The affected area is the leg and arm. Texture is reported as flat. The photo was captured at an angle. The patient reported no systemic symptoms. Skin tone: Fitzpatrick phototype III; non-clinician graders estimated MST 2. Reported duration is one to three months: 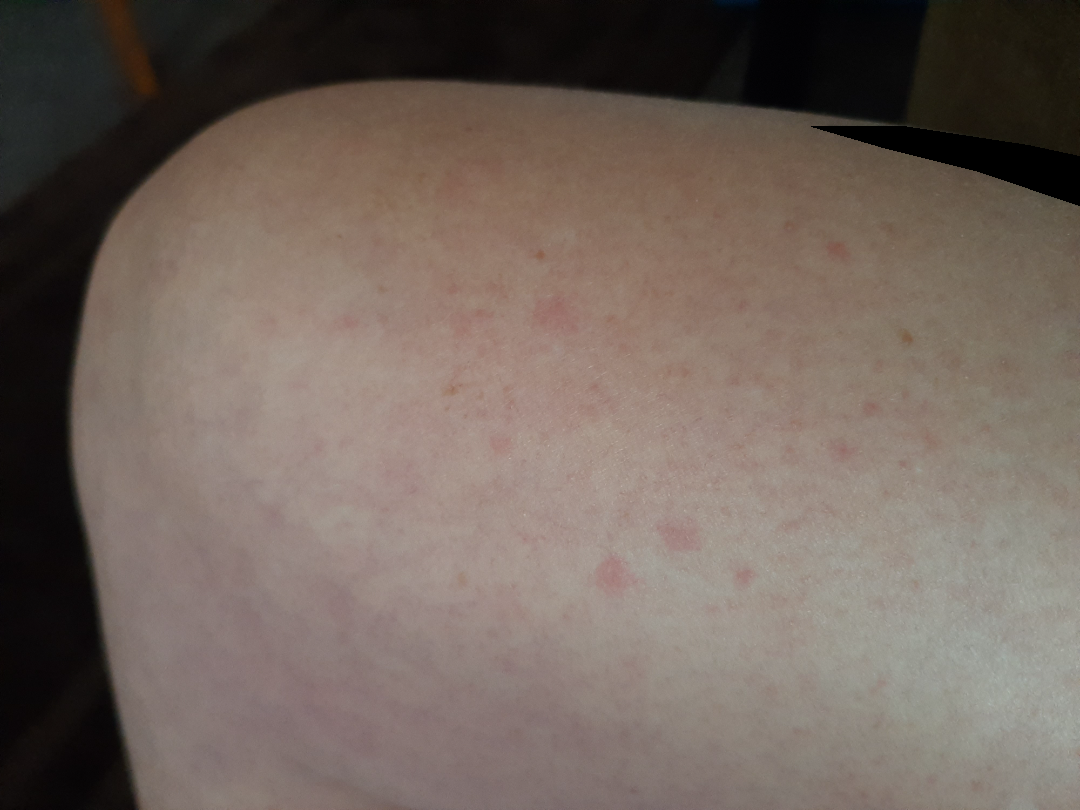Findings:
The dermatologist could not determine a likely condition from the photograph alone.